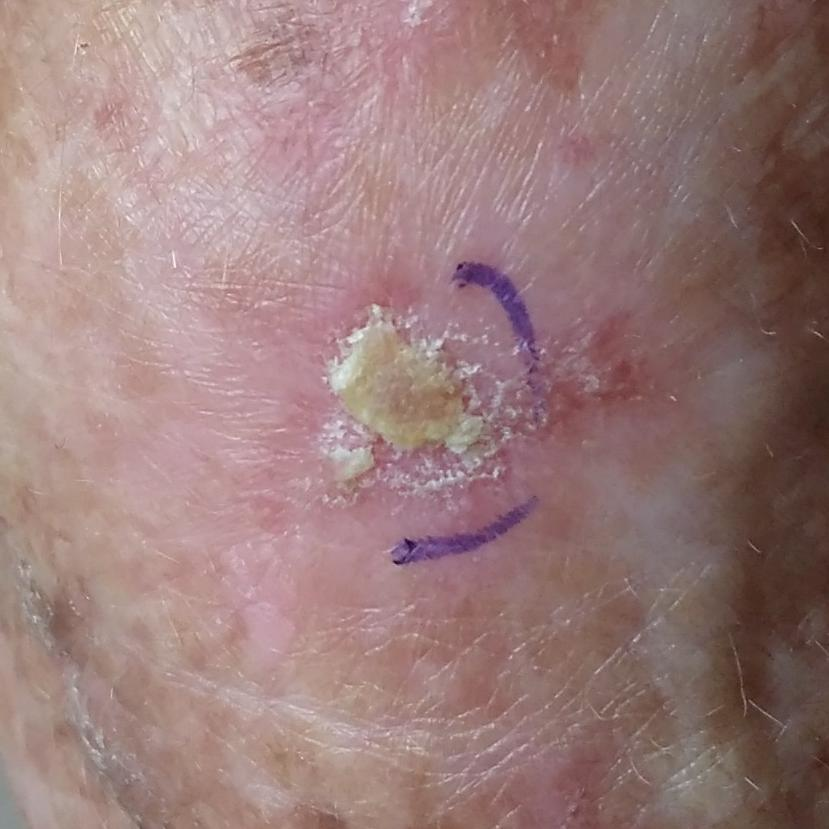Skin type II.
A clinical photograph of a skin lesion.
A female patient age 79.
By history, no tobacco use and no pesticide exposure.
The lesion is located on a hand.
The lesion measures approximately 15 × 10 mm.
The patient describes that the lesion itches, is elevated, and has grown, but has not changed.
The consensus clinical diagnosis was an actinic keratosis.